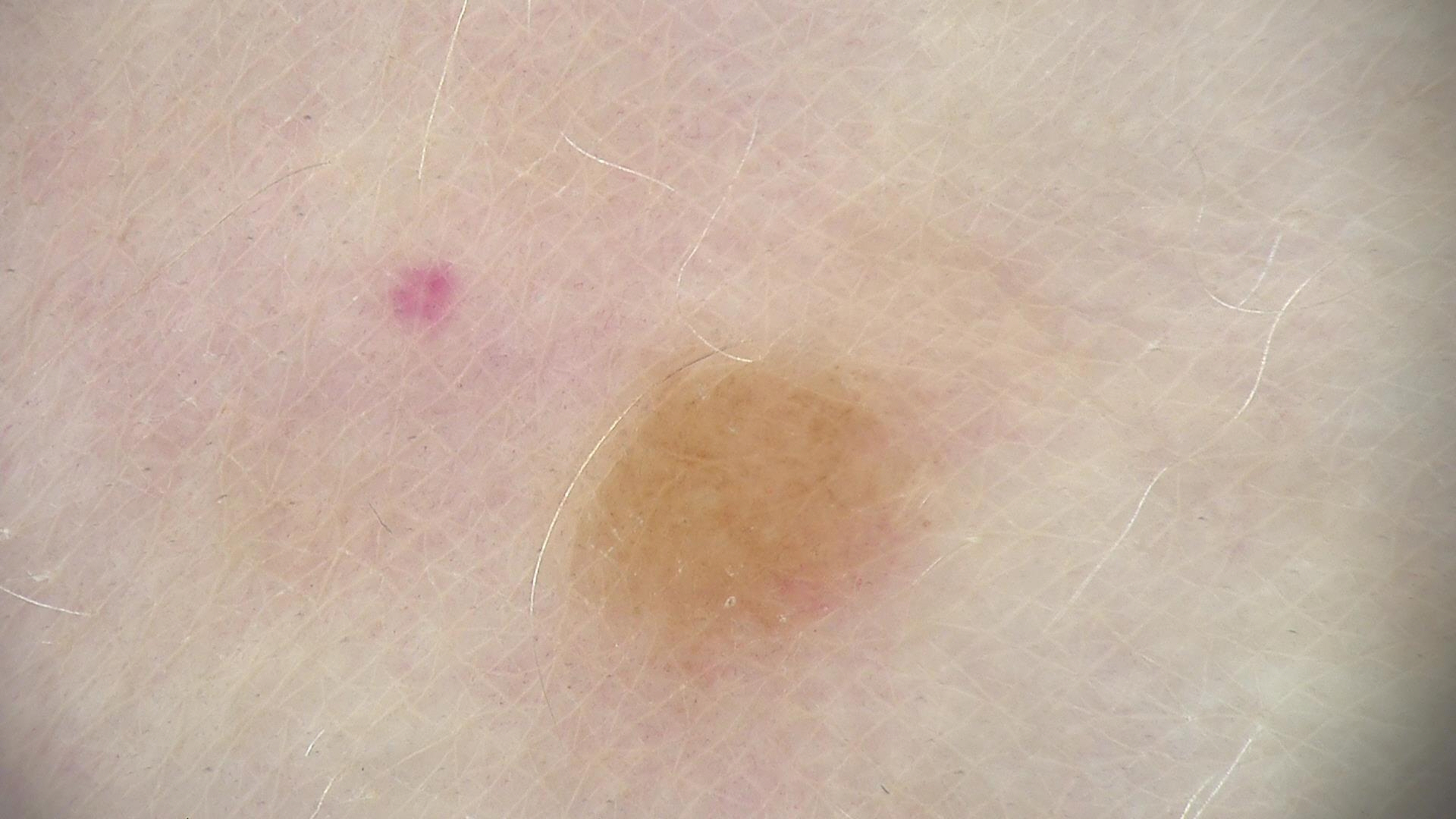Diagnosed as a junctional nevus.